A dermoscopy image of a single skin lesion:
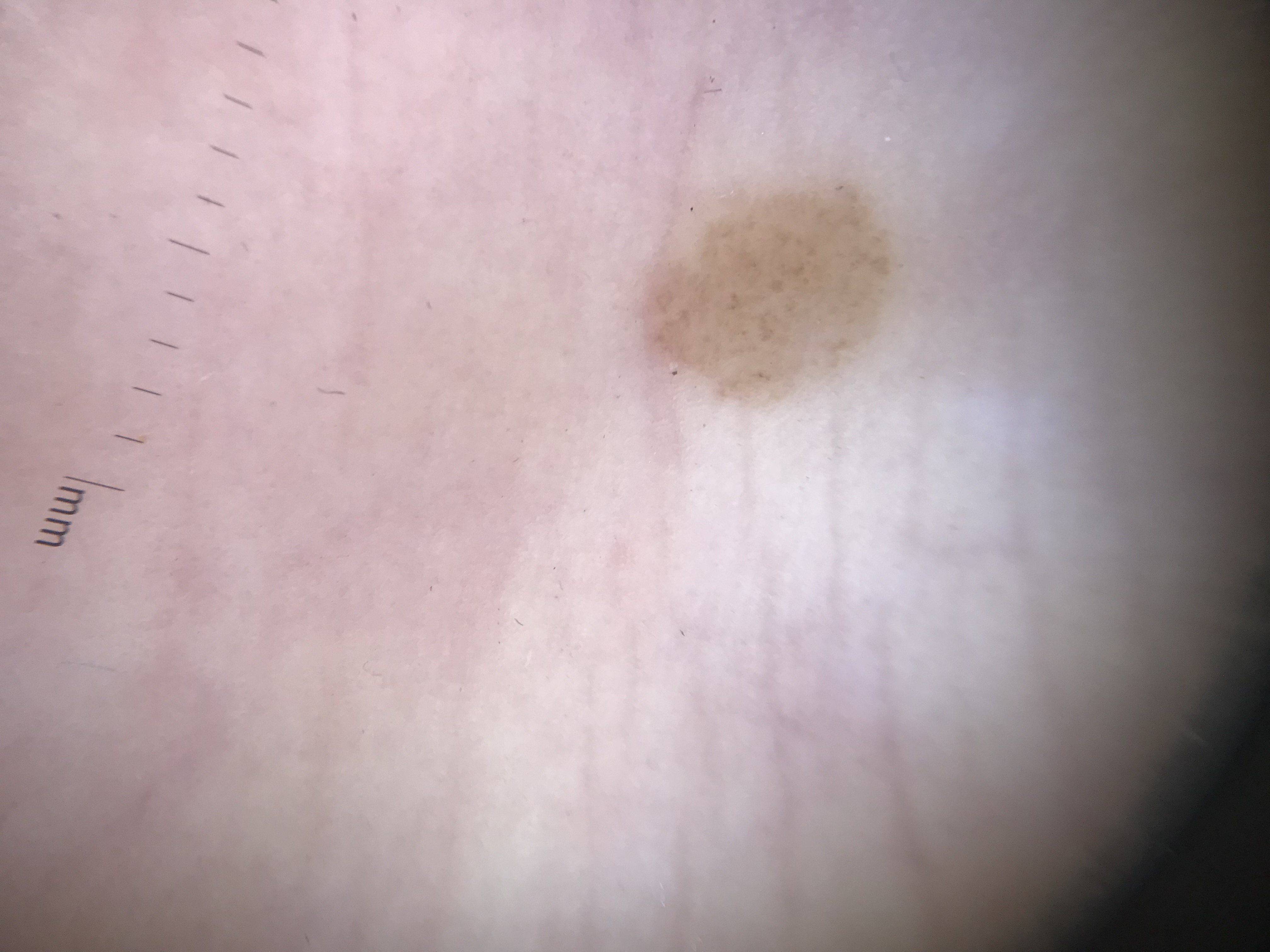class = acral dysplastic junctional nevus (expert consensus).